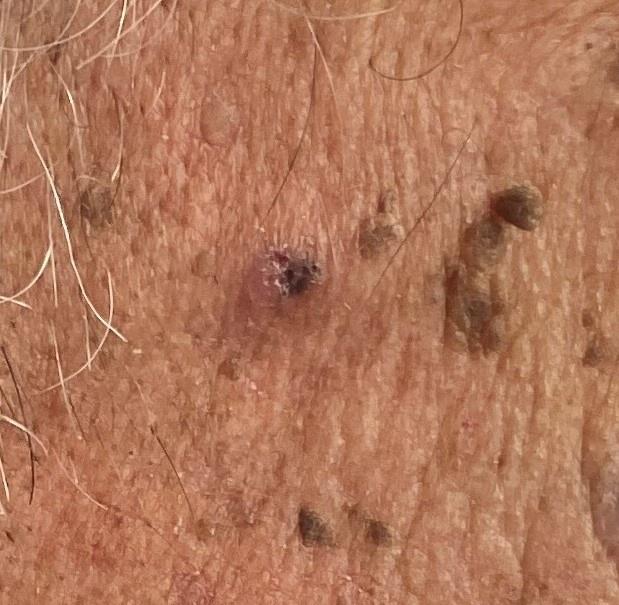Conclusion: On biopsy, the diagnosis was a basal cell carcinoma.